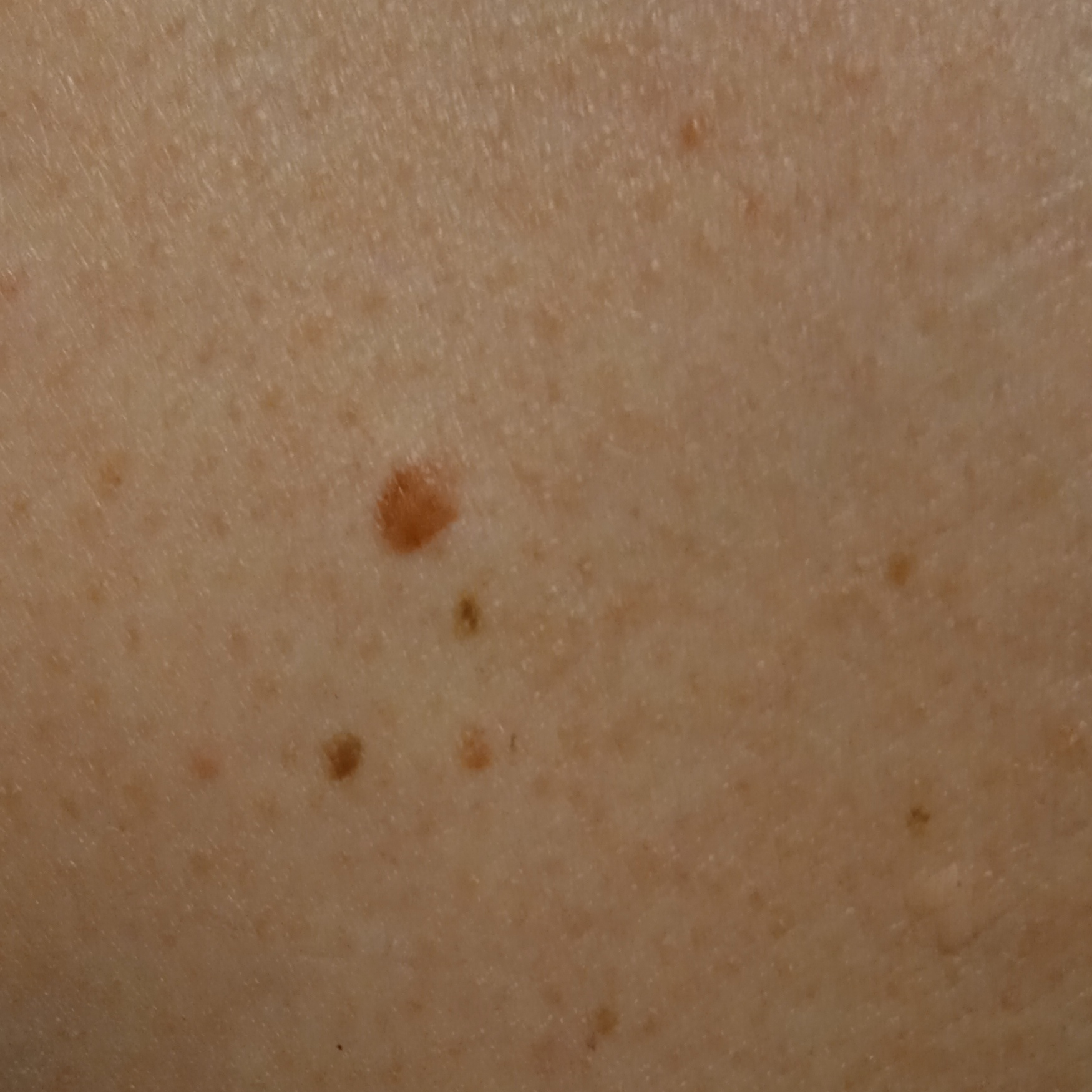- imaging — clinical photograph
- subject — male, age 65
- risk factors — a family history of skin cancer, immunosuppression, a personal history of skin cancer
- referral context — research study (no referral diagnosis)
- sun reaction — skin reddens painfully with sun exposure
- body site — the back
- size — 4.4 mm
- diagnosis — melanocytic nevus (dermatologist consensus)